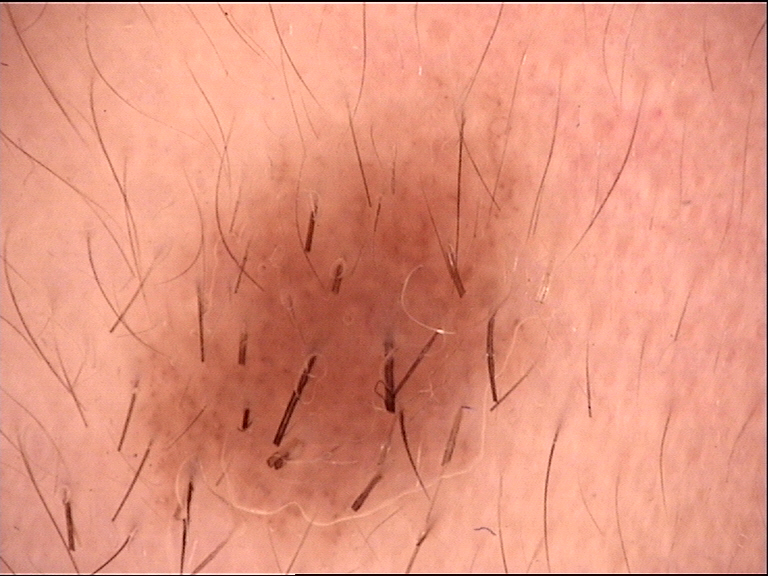A dermoscopy image of a single skin lesion. Consistent with a banal lesion — a Miescher nevus.